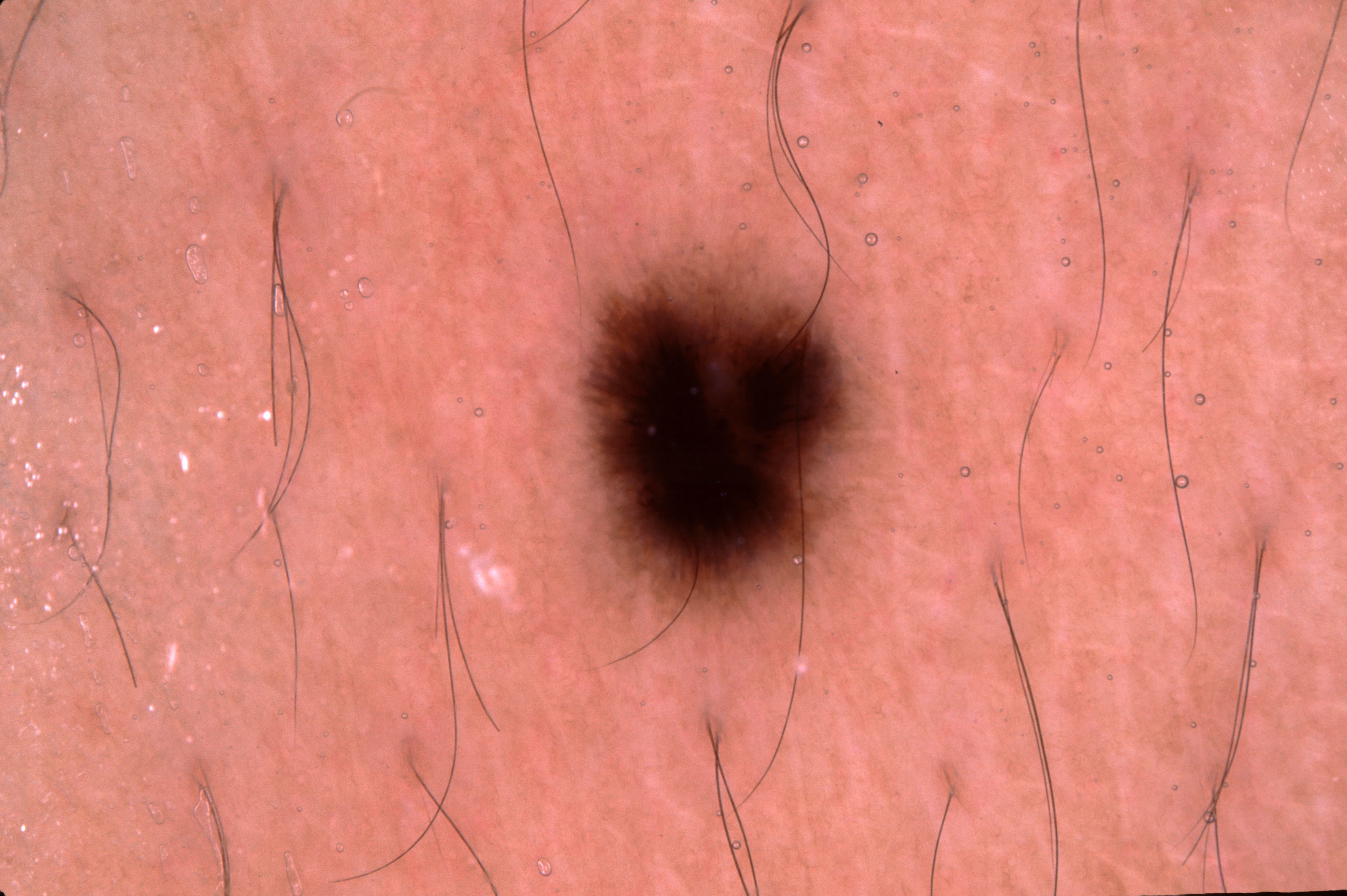<record>
  <image>
    <modality>dermoscopy</modality>
  </image>
  <patient>
    <sex>male</sex>
    <age_approx>20</age_approx>
  </patient>
  <dermoscopic_features>
    <present/>
    <absent>milia-like cysts, streaks, pigment network, negative network</absent>
  </dermoscopic_features>
  <lesion_location>
    <bbox_xyxy>565, 234, 870, 656</bbox_xyxy>
  </lesion_location>
  <lesion_extent>
    <approx_field_fraction_pct>9</approx_field_fraction_pct>
  </lesion_extent>
  <diagnosis>
    <name>melanocytic nevus</name>
    <malignancy>benign</malignancy>
    <lineage>melanocytic</lineage>
    <provenance>clinical</provenance>
  </diagnosis>
</record>